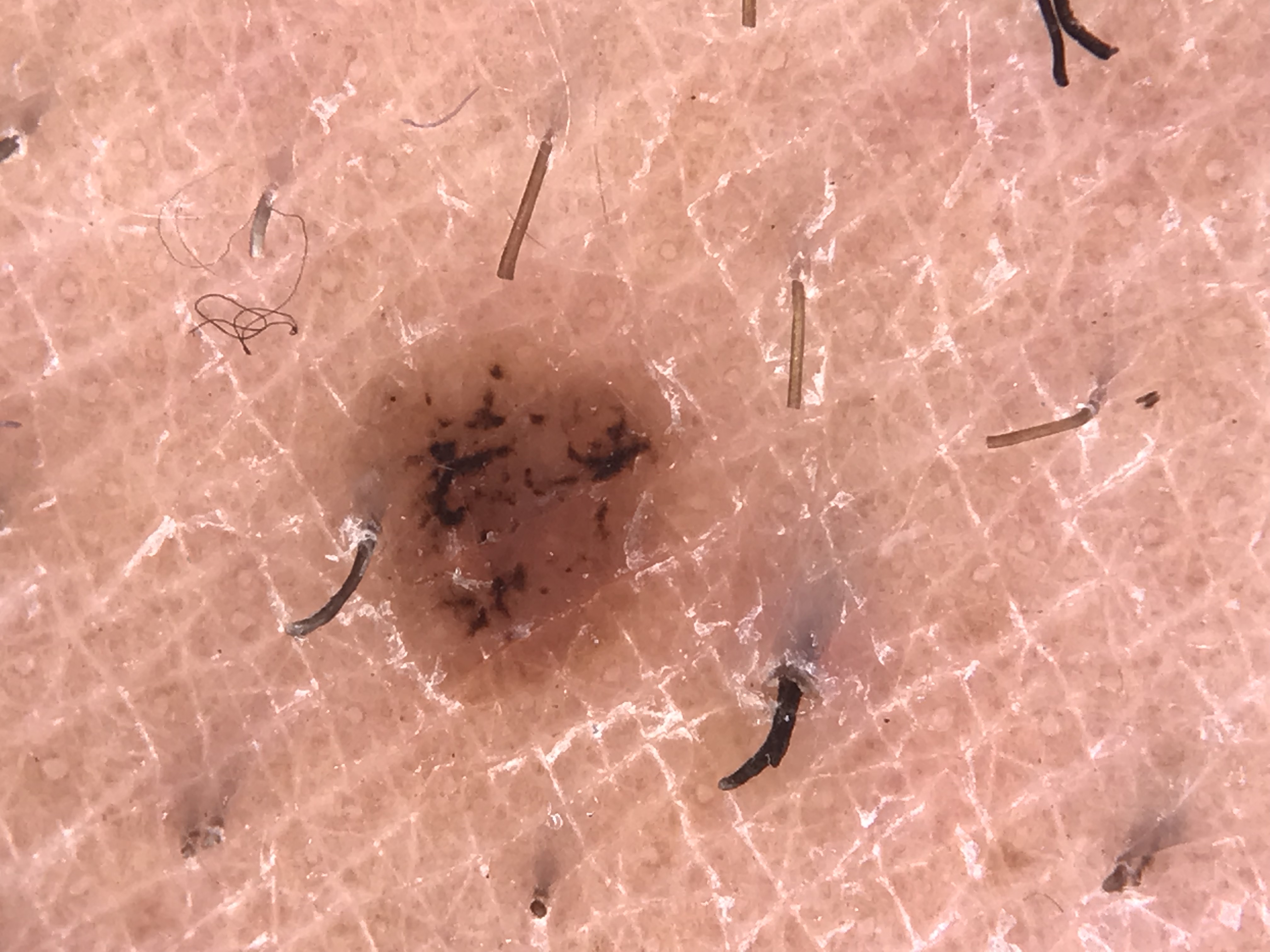Conclusion: The diagnosis was a dysplastic junctional nevus.